The patient considered this a rash. No constitutional symptoms were reported. The lesion involves the leg. The lesion is described as rough or flaky and raised or bumpy. The condition has been present for less than one week. Male contributor, age 40–49. This image was taken at an angle: 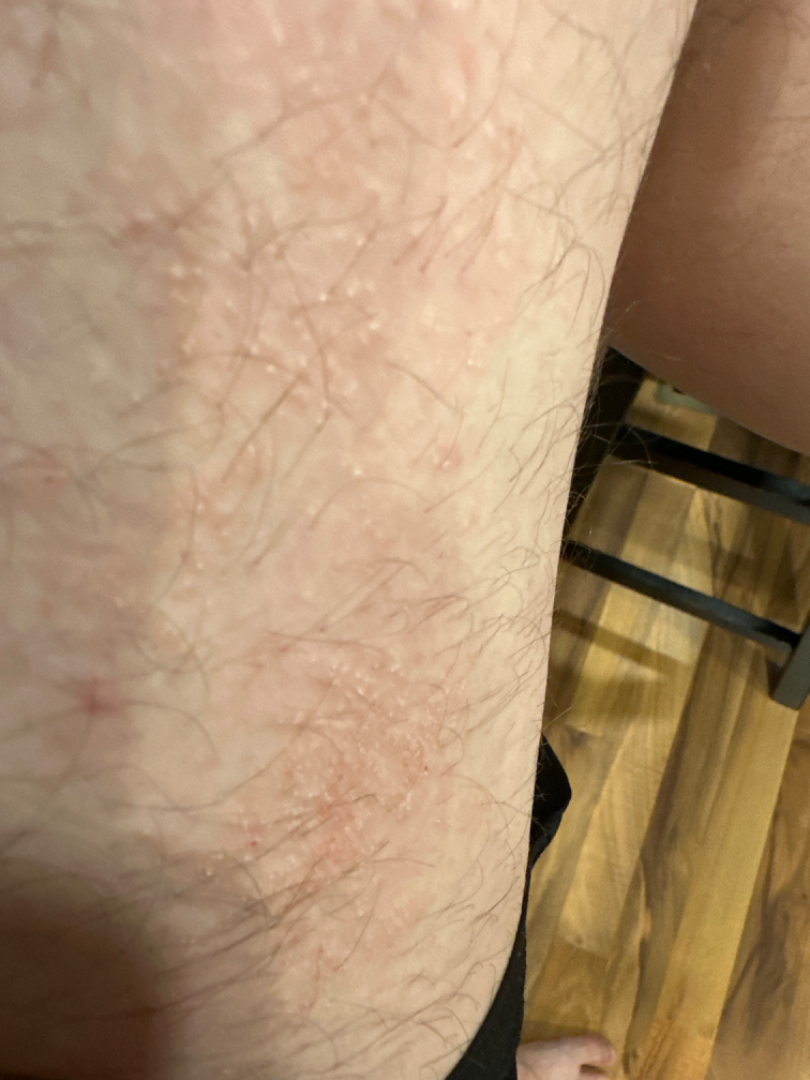  differential:
    leading:
      - Eczema
    considered:
      - Acute and chronic dermatitis
    unlikely:
      - Tinea